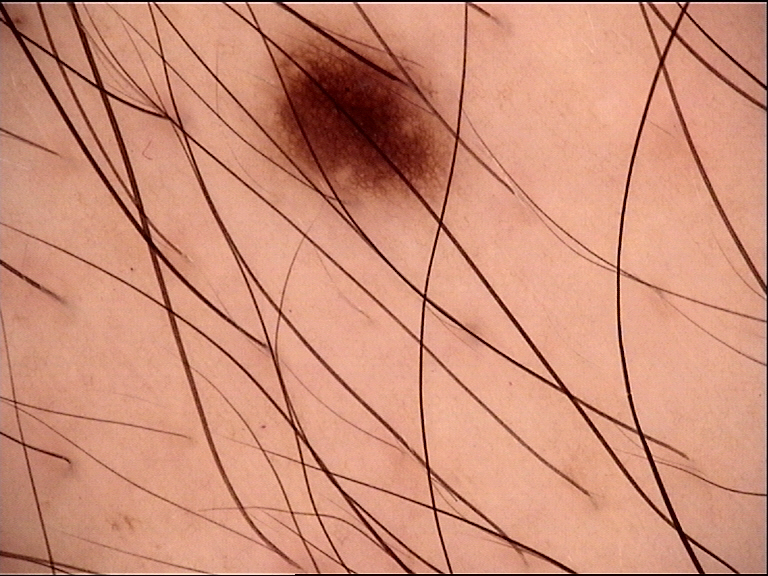- diagnosis · junctional nevus (expert consensus)